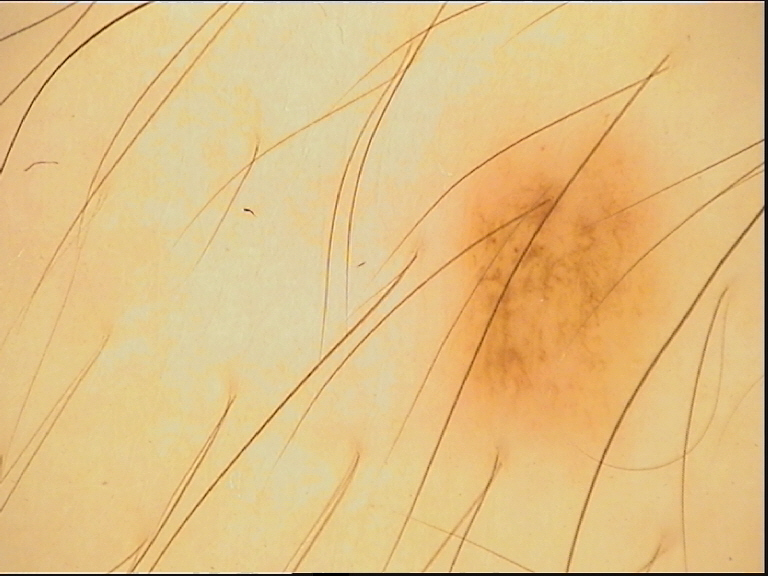image type = dermoscopy, label = dysplastic junctional nevus (expert consensus).